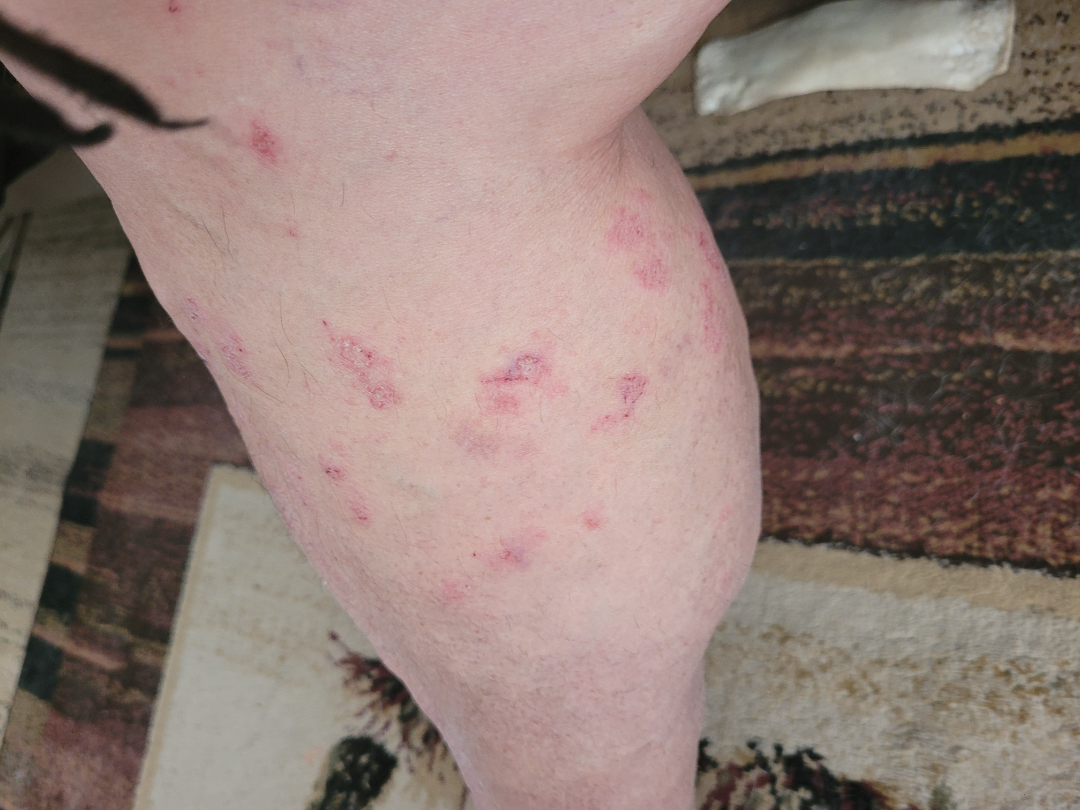clinical impression: Eczema (most likely); Pityriasis lichenoides (possible).